Close-up view. The affected area is the arm, top or side of the foot and leg — 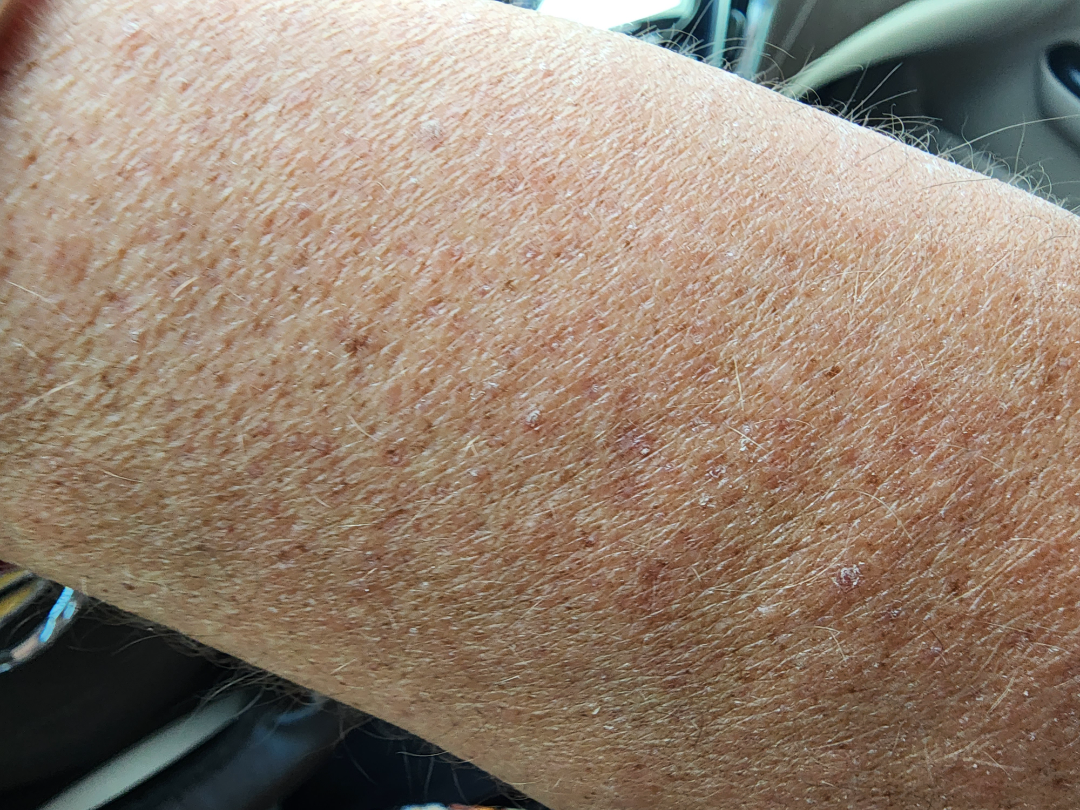On teledermatology review: Actinic Keratosis (100%).